Self-categorized by the patient as skin that appeared healthy to them · the photograph was taken at an angle · the affected area is the arm · the lesion is associated with itching · texture is reported as raised or bumpy · reported duration is about one day.
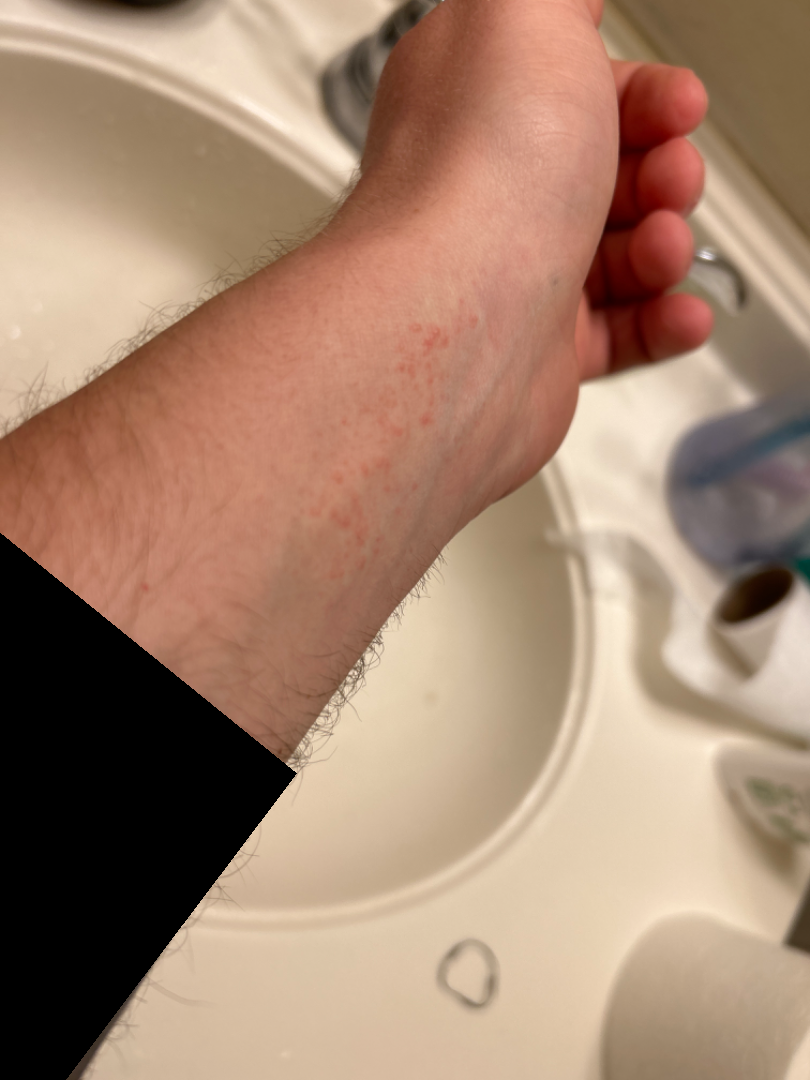{"assessment": "not assessable"}